A close-up photograph · the subject is female.
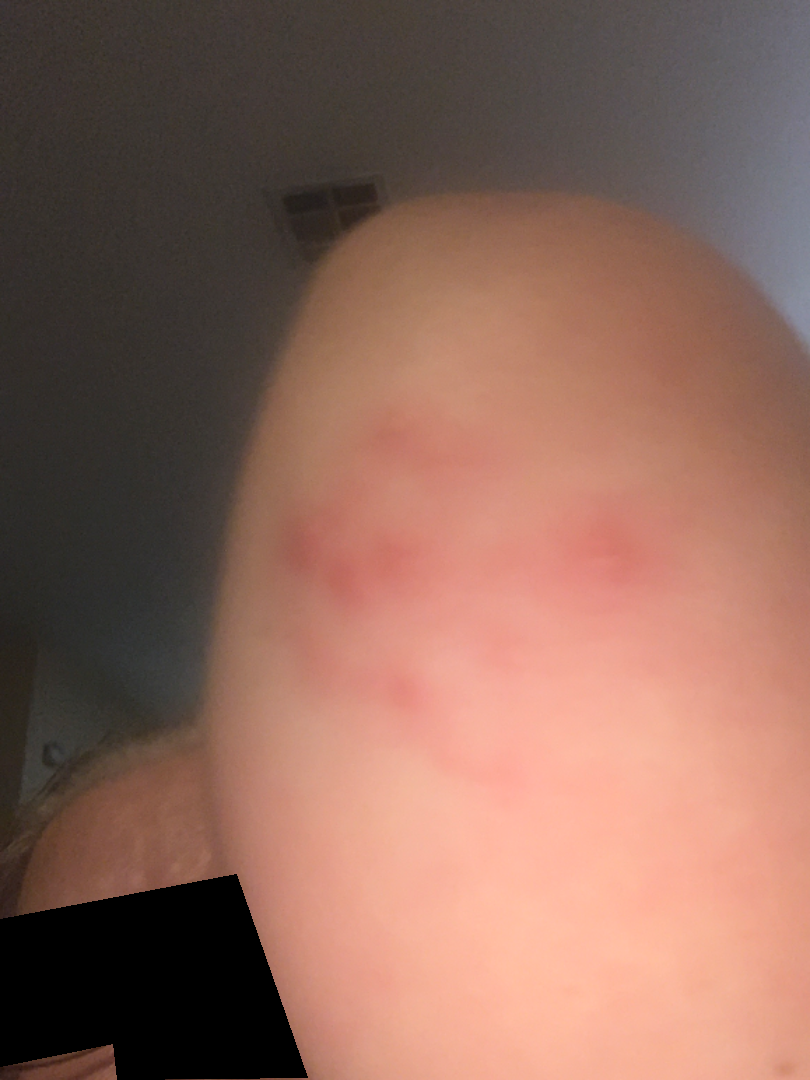assessment: could not be assessed.